A clinical photograph showing a skin lesion; the patient says their skin reddens with sun exposure; a female patient 50 years of age; the patient describes having a moderate number of moles; collected as part of a research study, without a referral diagnosis:
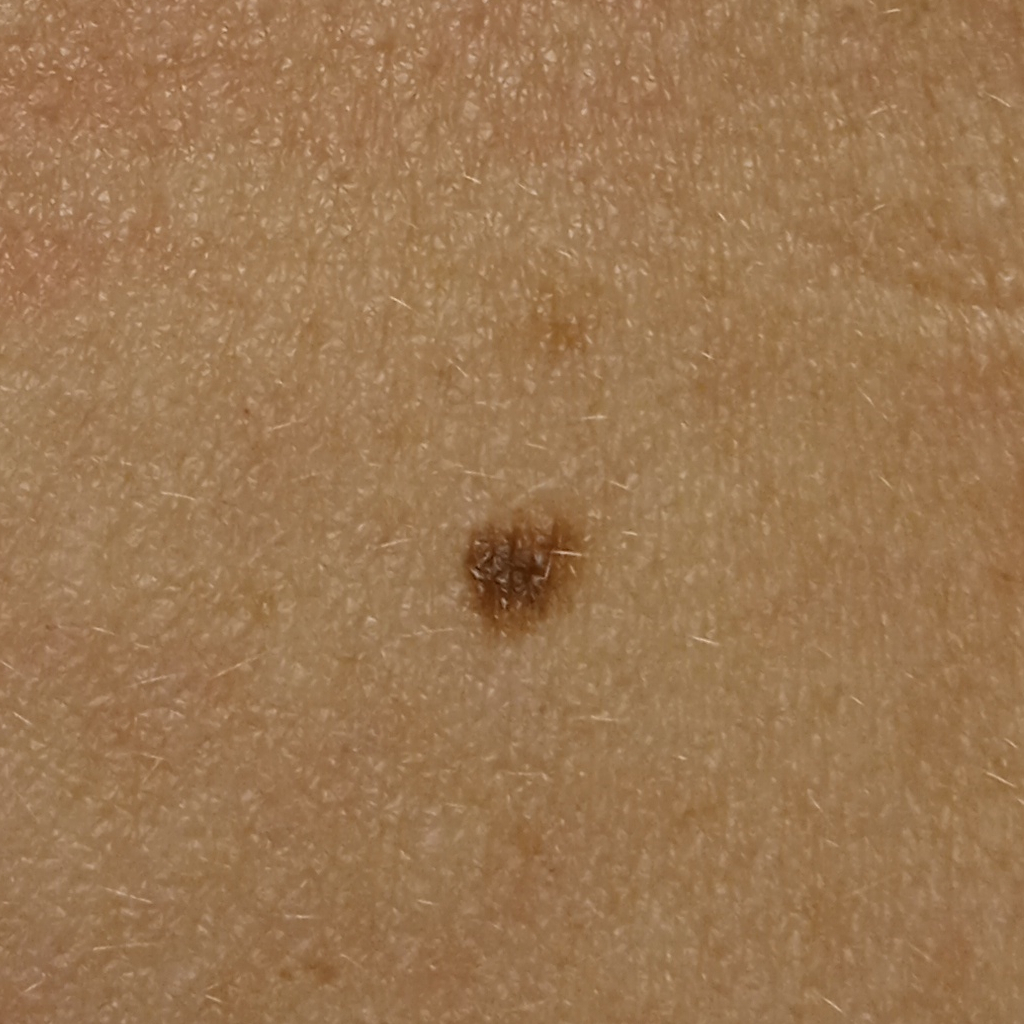Q: Where is the lesion?
A: the torso
Q: How large is the lesion?
A: 5.4 mm
Q: What was the diagnosis?
A: melanocytic nevus (dermatologist consensus)